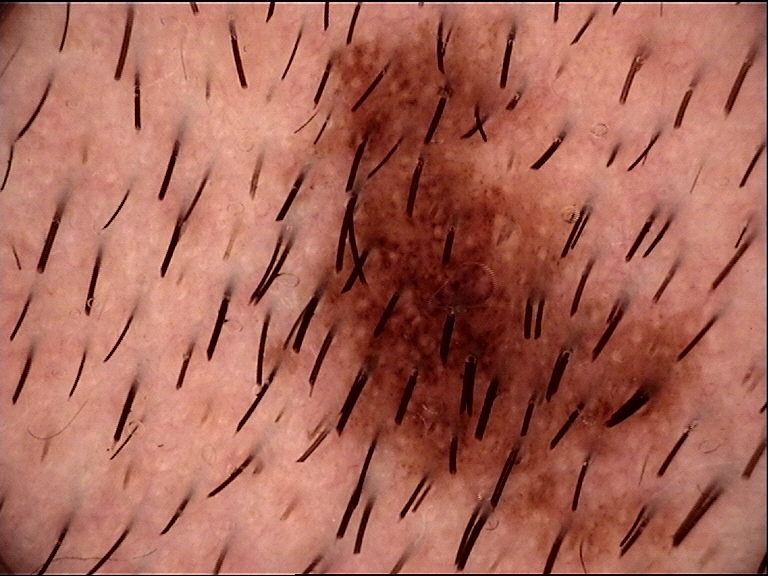<case>
<image>dermoscopy</image>
<diagnosis>
<name>dysplastic junctional nevus</name>
<code>jd</code>
<malignancy>benign</malignancy>
<super_class>melanocytic</super_class>
<confirmation>expert consensus</confirmation>
</diagnosis>
</case>